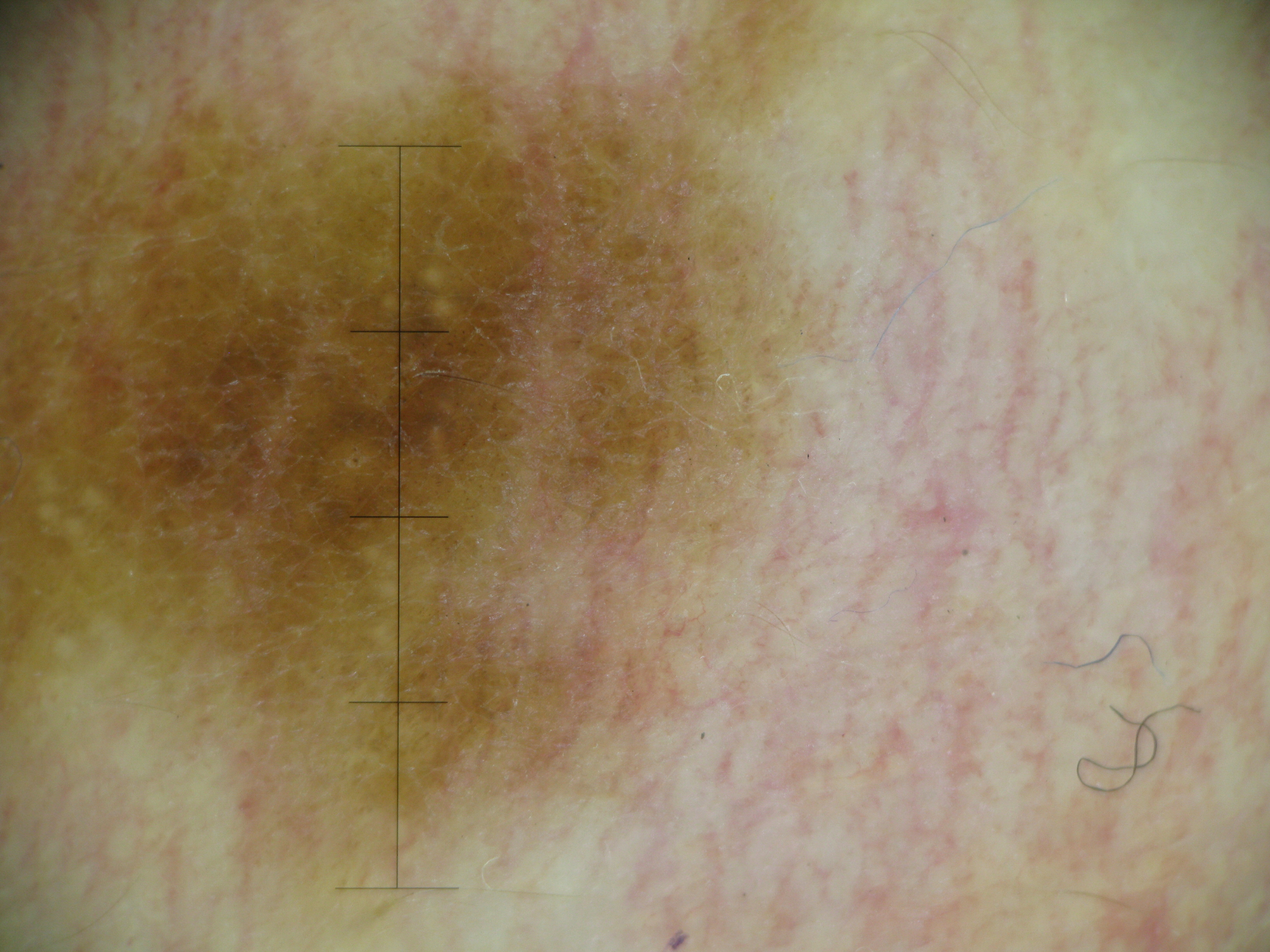Conclusion: Consistent with a dysplastic junctional nevus.